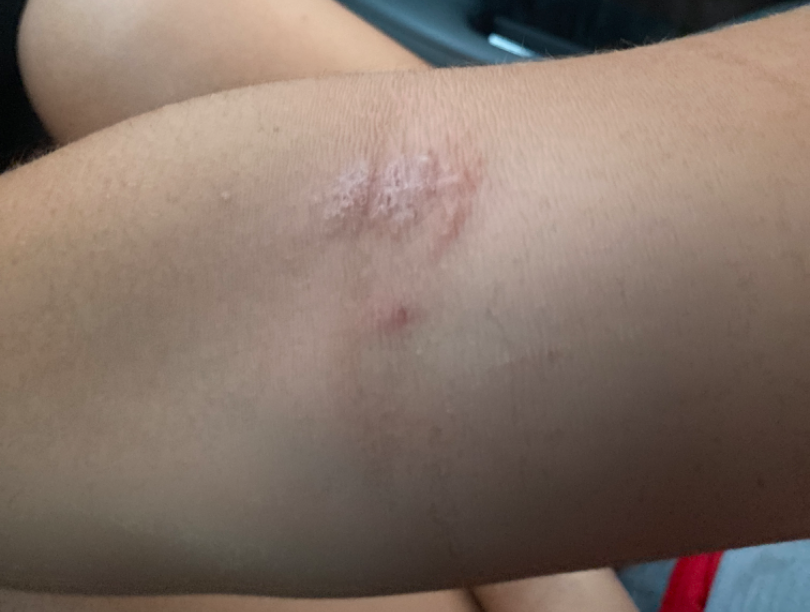History:
The photo was captured at an angle.
Impression:
On photographic review by a dermatologist, in keeping with Eczema.